A dermoscopic view of a skin lesion.
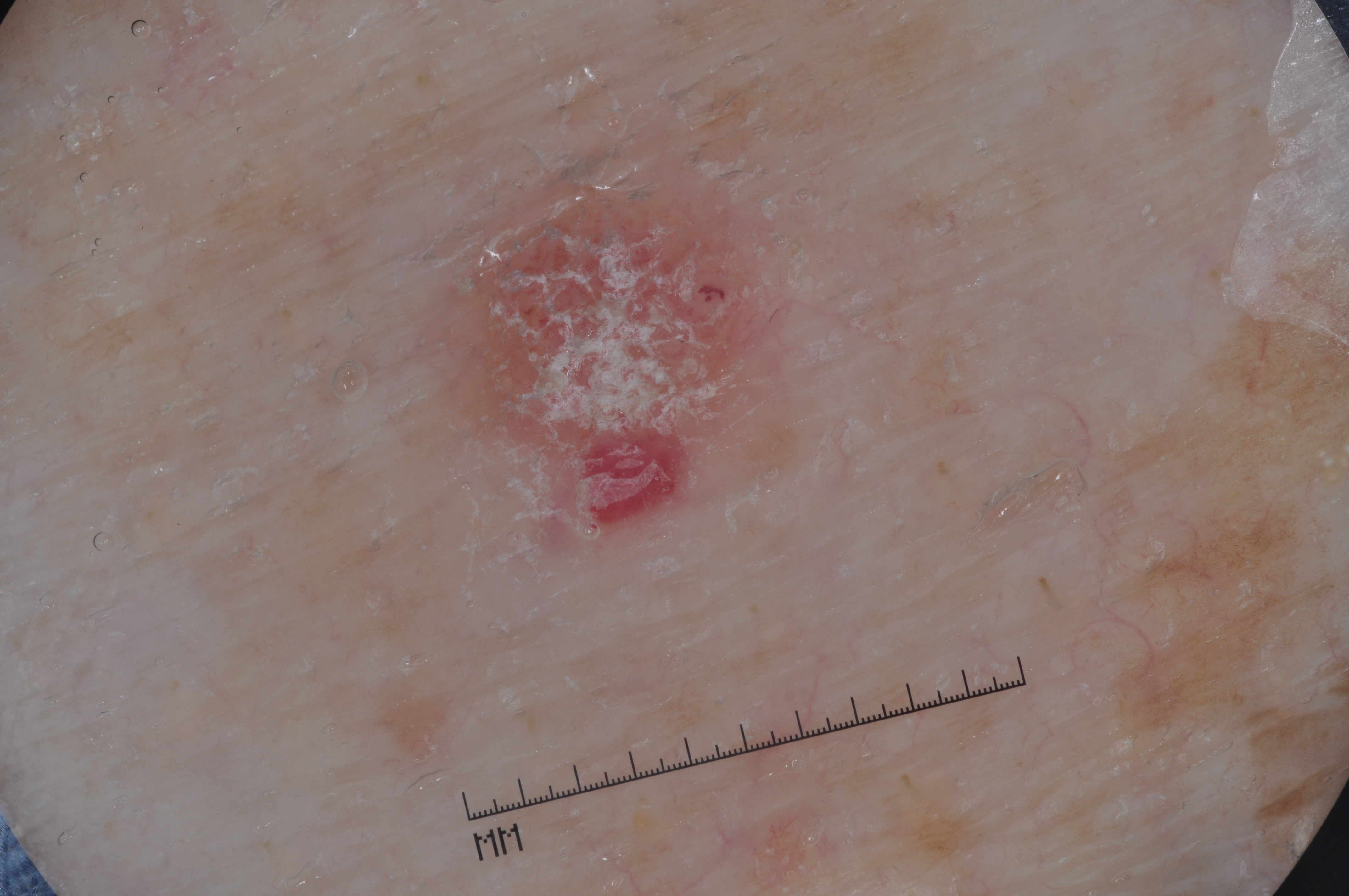– bounding box — 396/160/812/563
– assessment — a seborrheic keratosis, a benign skin lesion